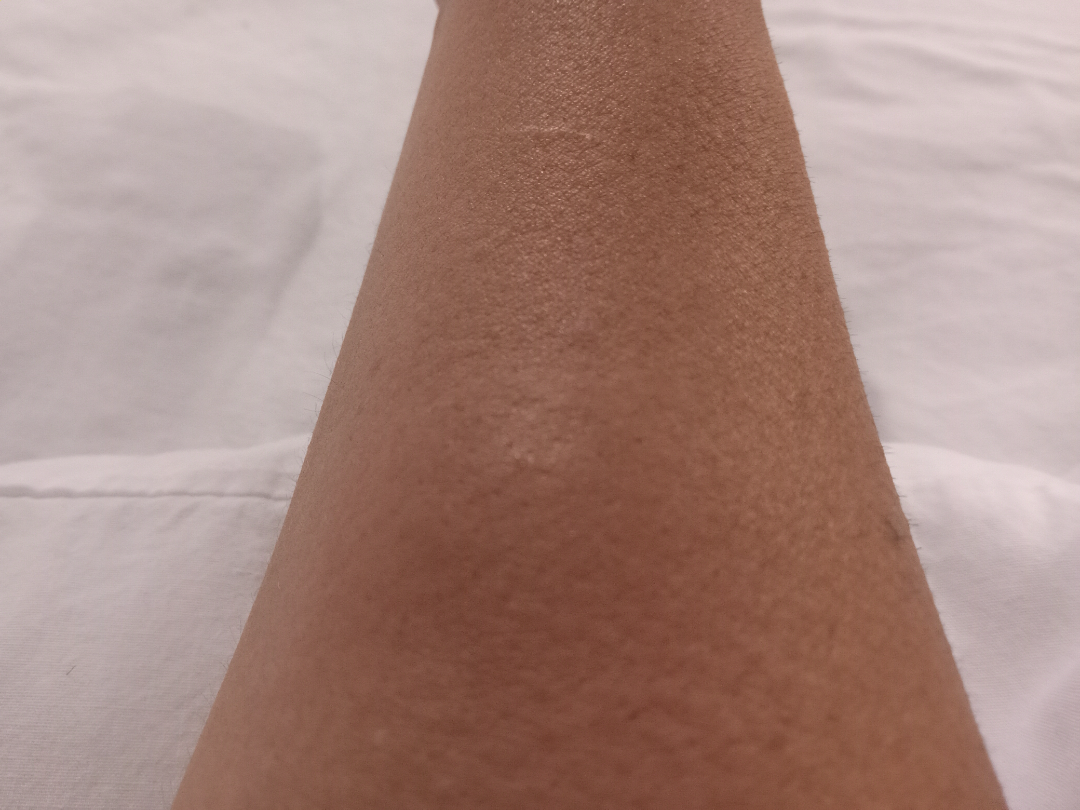assessment: none discernible.